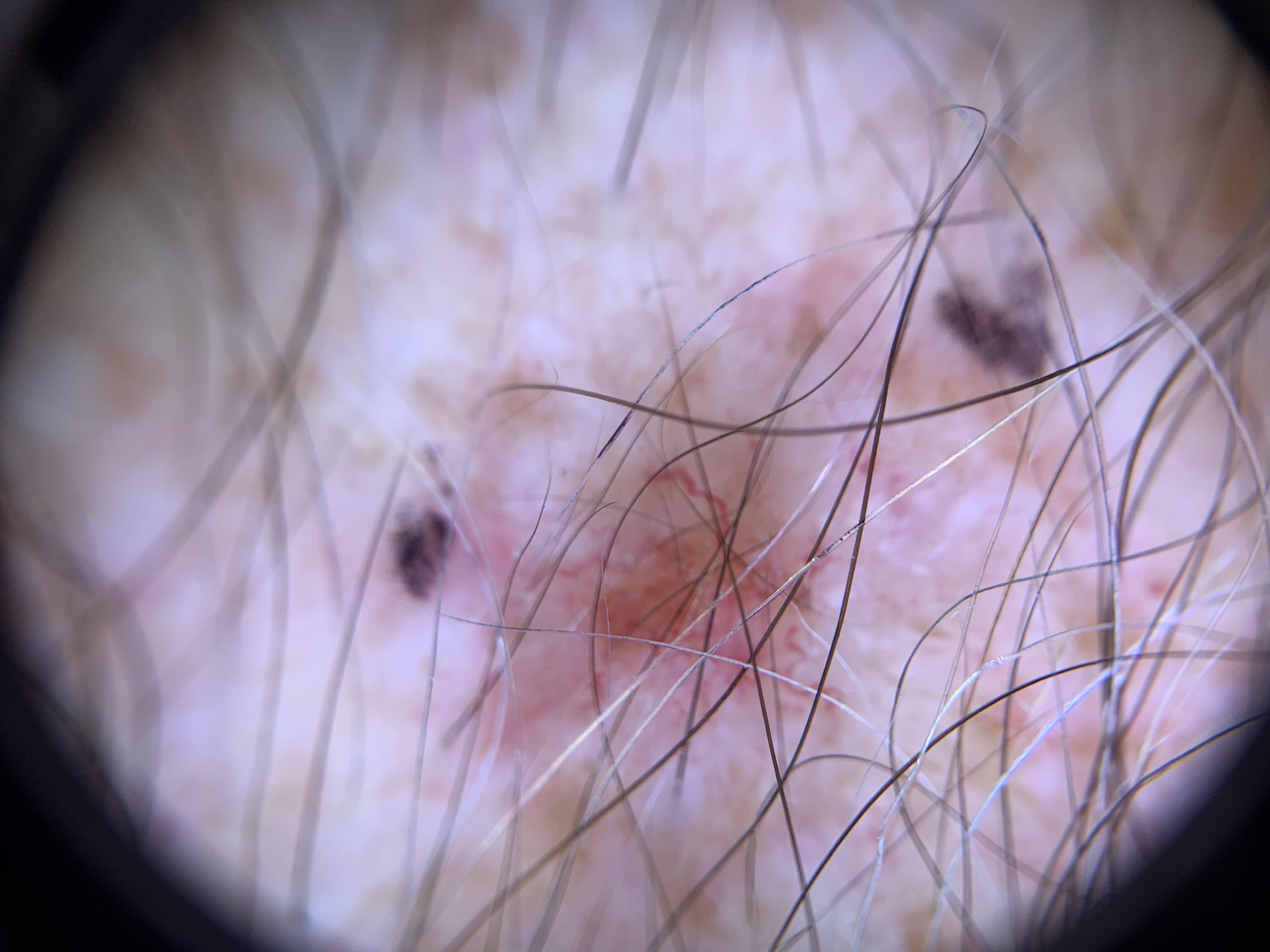patient: male, roughly 70 years of age; modality: dermoscopic image; FST: I; diagnosis: Basal cell carcinoma (biopsy-proven).